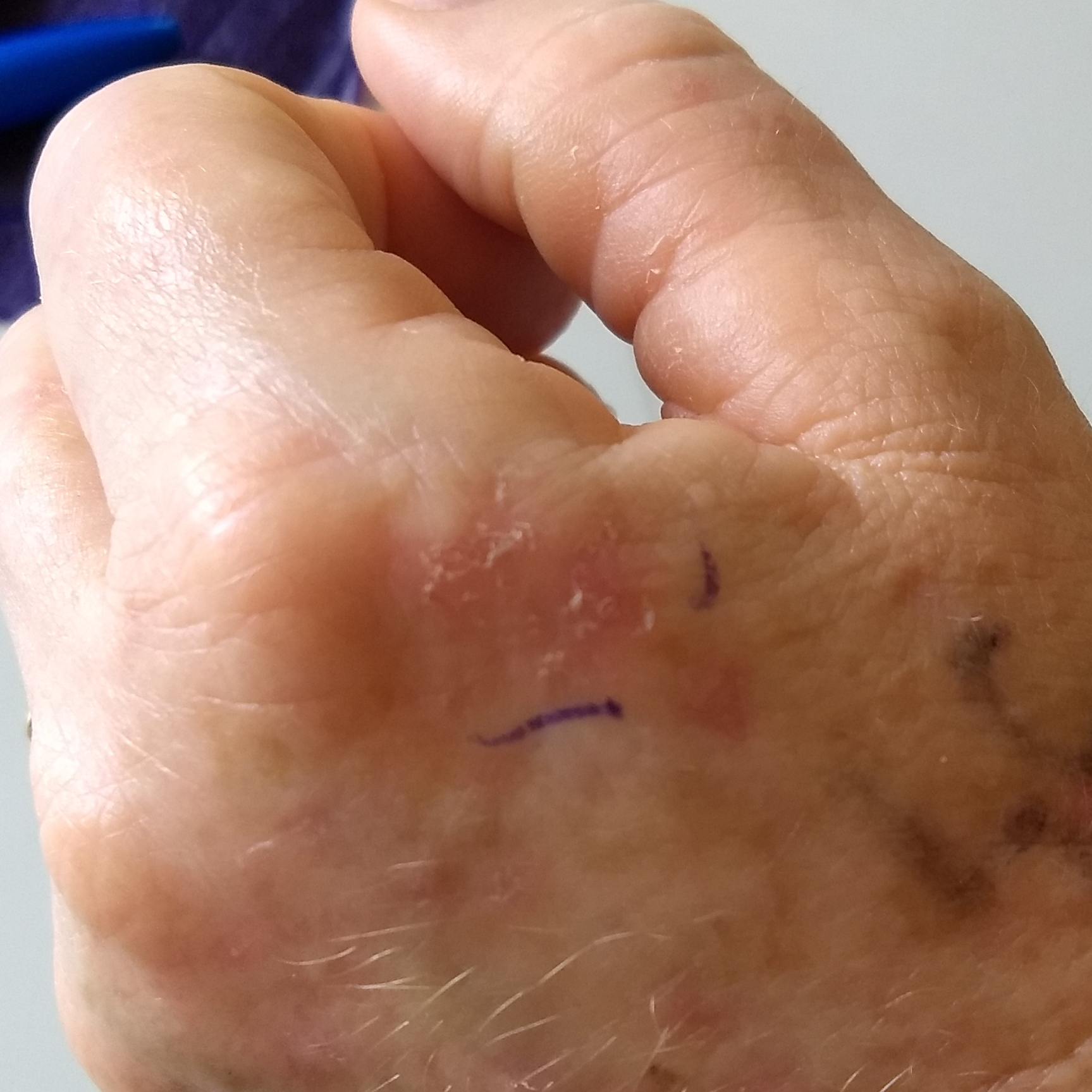skin phototype=I; risk factors=prior skin cancer (patient or family); subject=female, in their 50s; image=smartphone clinical photo; anatomic site=a hand; symptoms=itching; diagnostic label=actinic keratosis (clinical consensus).